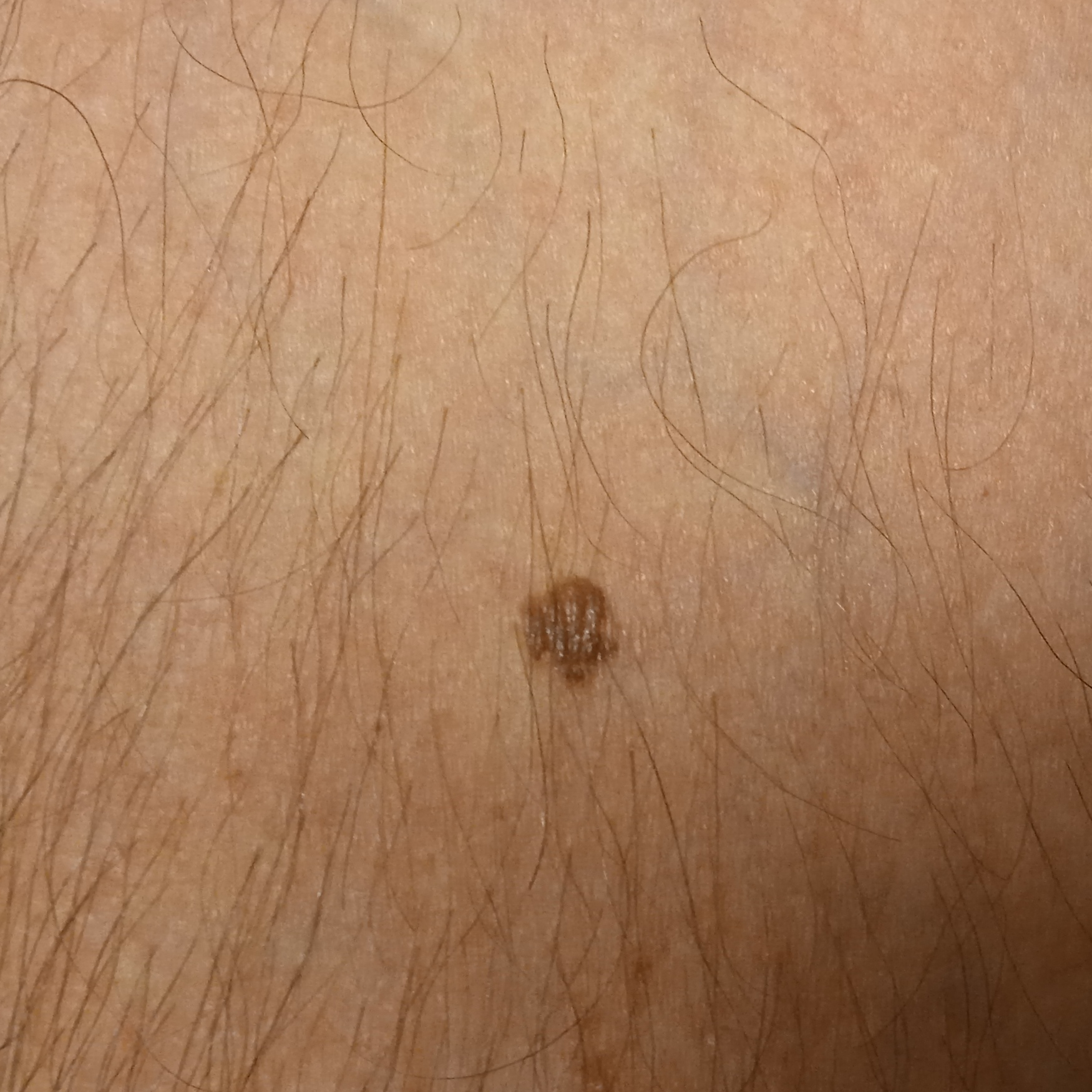| field | value |
|---|---|
| diagnostic label | melanocytic nevus (dermatologist consensus) |